The patient is a female aged 60–69; located on the leg; the photograph was taken at an angle: 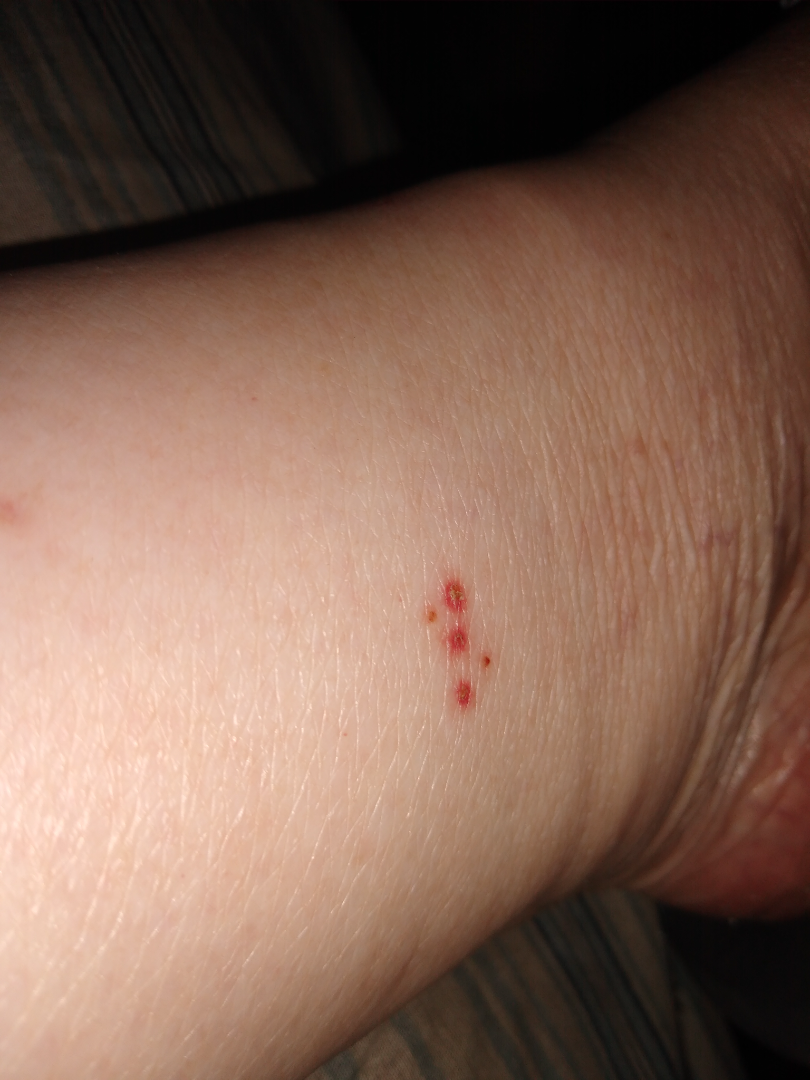Clinical context:
Self-categorized by the patient as a rash. The lesion is described as fluid-filled. Skin tone: Fitzpatrick skin type III. The patient did not report lesion symptoms.
Assessment:
Favoring Insect Bite; an alternative is Impetigo; a more distant consideration is Folliculitis; less probable is Viral infection of skin; less likely is Allergic Contact Dermatitis.